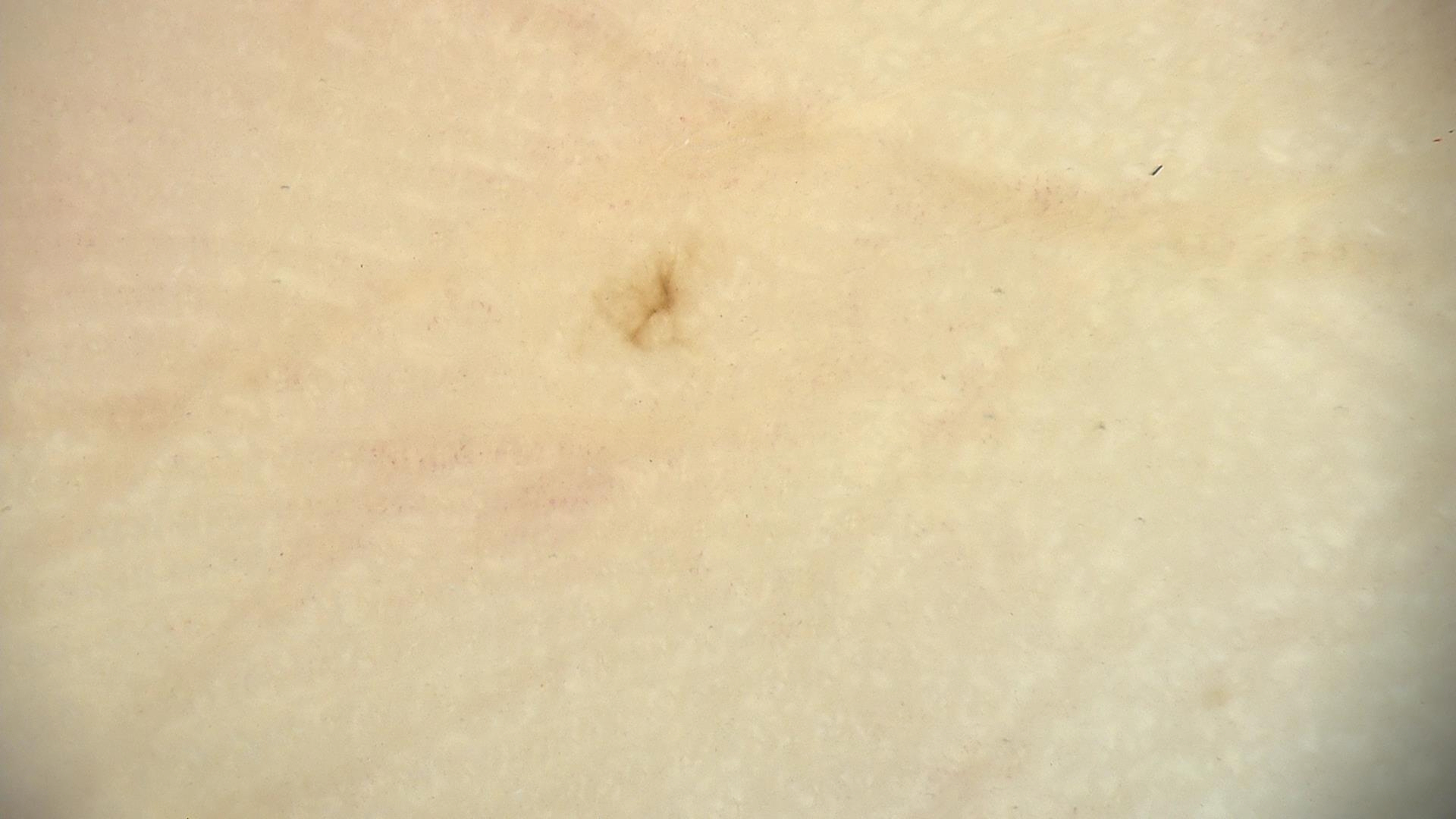The diagnosis was an acral dysplastic junctional nevus.